The photograph was taken at a distance. Skin tone: lay reviewers estimated MST 4 or 6 (two reviewer pools disagreed) — 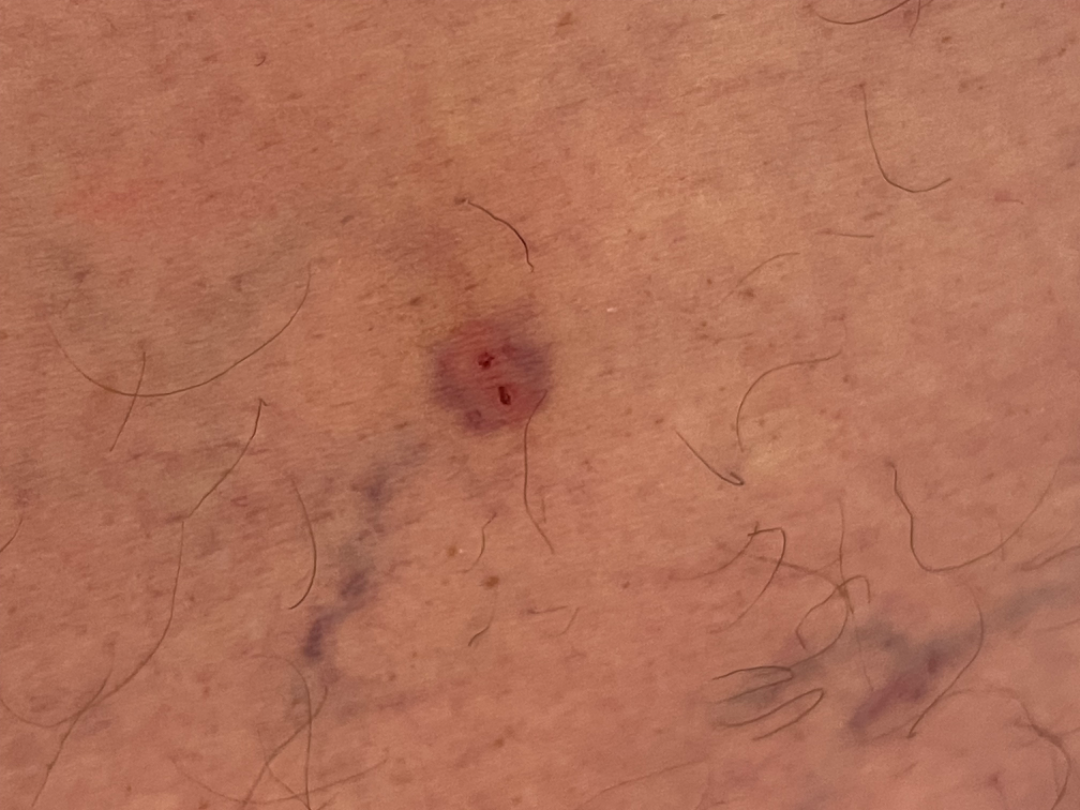Review:
The case was indeterminate on photographic review.